The patient considered this skin that appeared healthy to them, texture is reported as raised or bumpy, the leg is involved, skin tone: Fitzpatrick skin type II; lay reviewers estimated Monk skin tone scale 3, no relevant systemic symptoms, a close-up photograph, the condition has been present for less than one week, the patient notes itching.
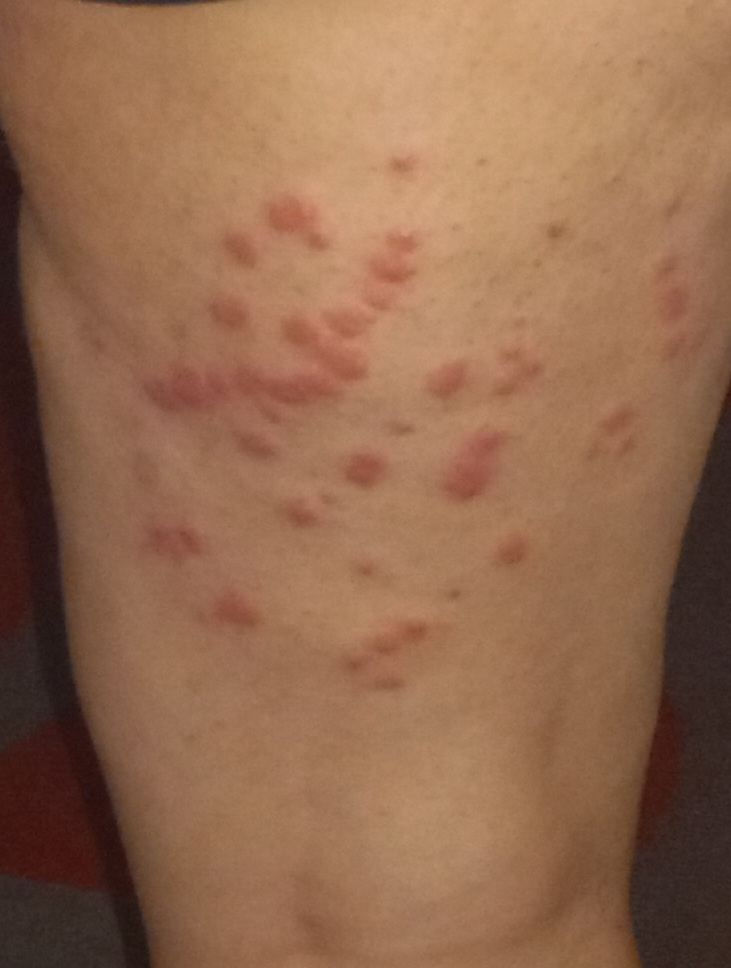Case summary:
– differential diagnosis — in keeping with Insect Bite